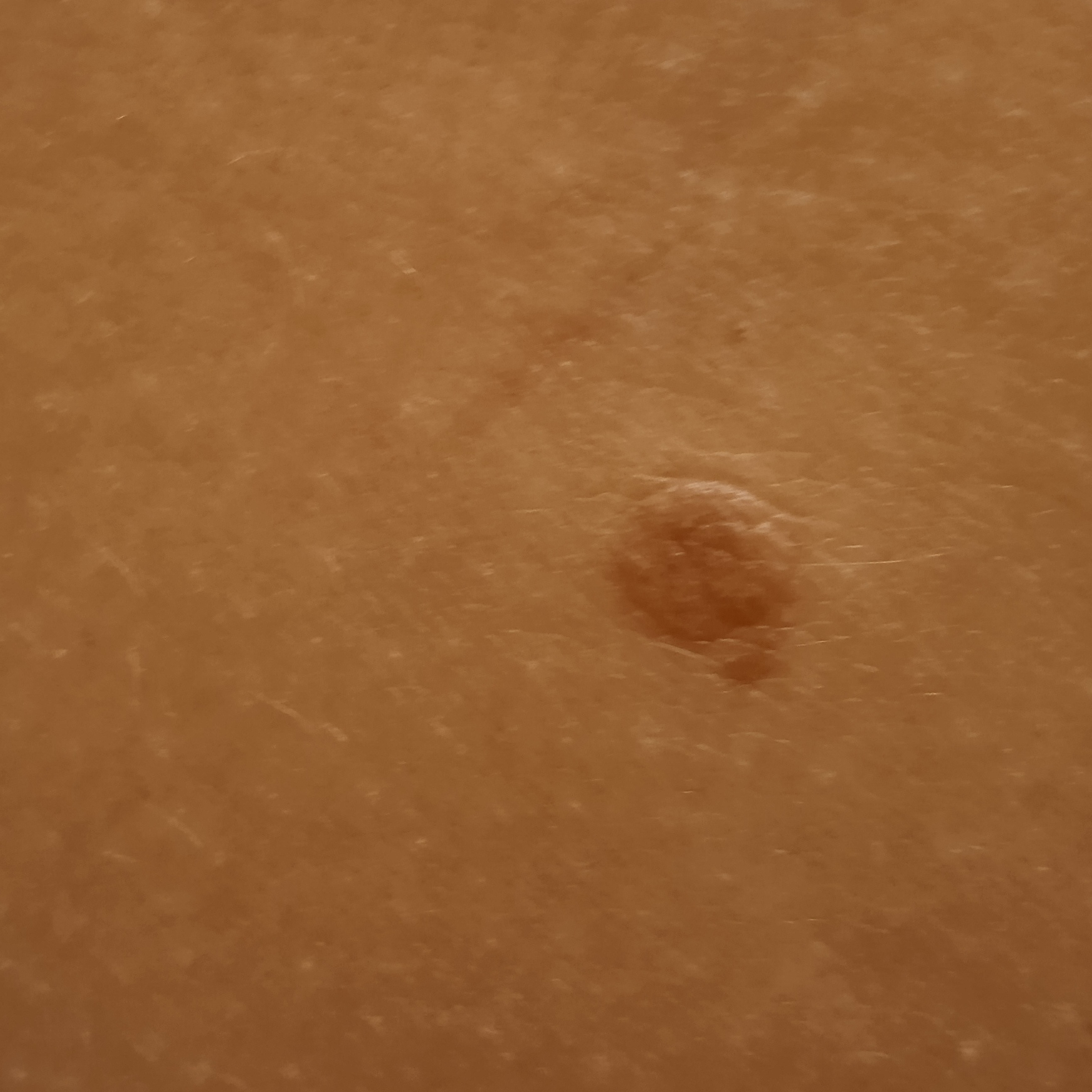The reviewing dermatologists could not reach a confident diagnosis. Case:
* nevus count — a moderate number of melanocytic nevi
* patient — female, 47 years old
* relevant history — a history of sunbed use, no immunosuppression, no family history of skin cancer